The subject is a female aged around 60 · a skin lesion imaged with a dermatoscope — 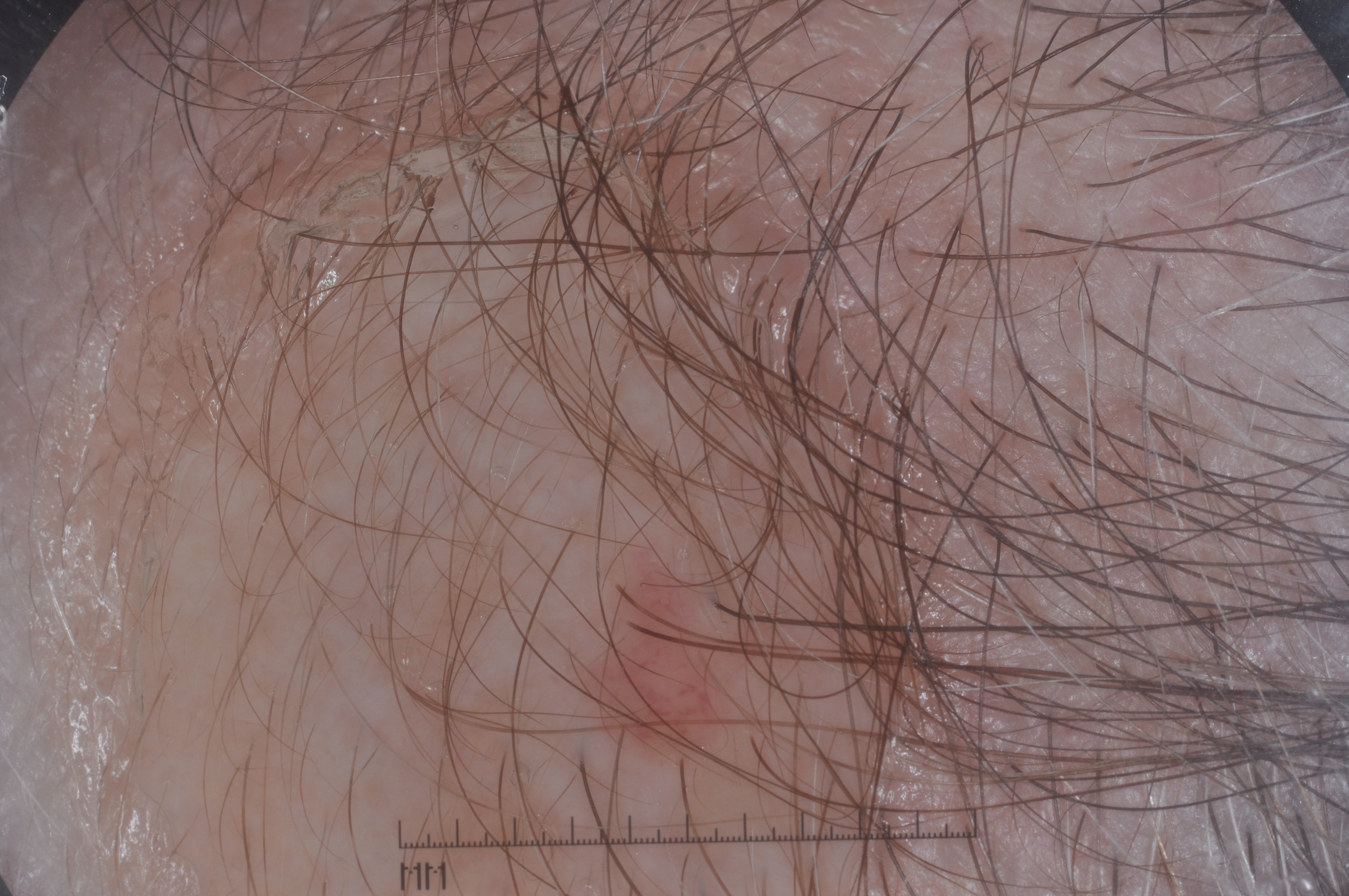Q: How much of the field does the lesion occupy?
A: small
Q: What is the lesion's bounding box?
A: [580, 546, 729, 773]
Q: Which assessed dermoscopic features were absent?
A: pigment network, negative network, streaks, and milia-like cysts
Q: What is this lesion?
A: a melanocytic nevus